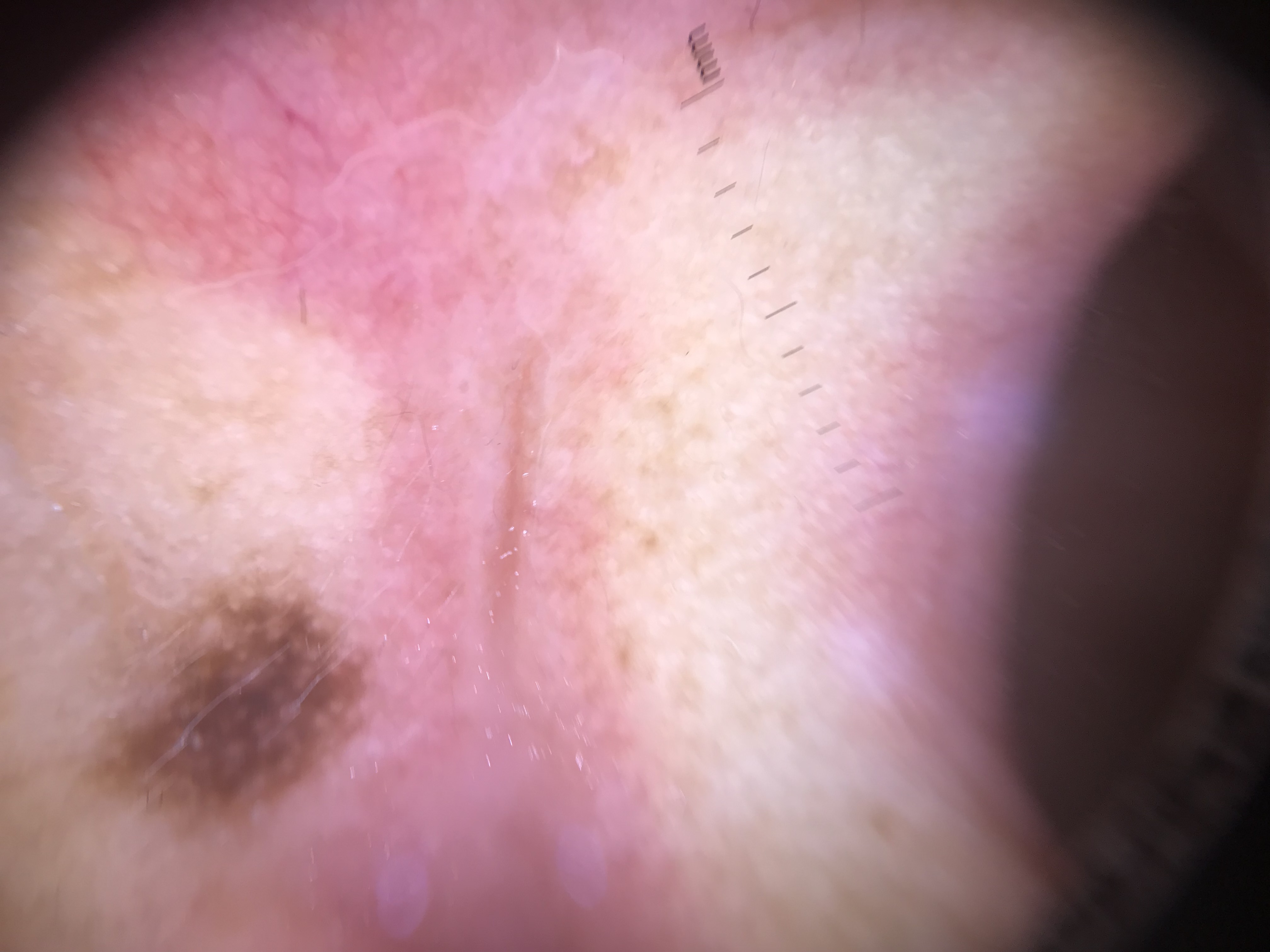label: acral dysplastic junctional nevus (expert consensus).